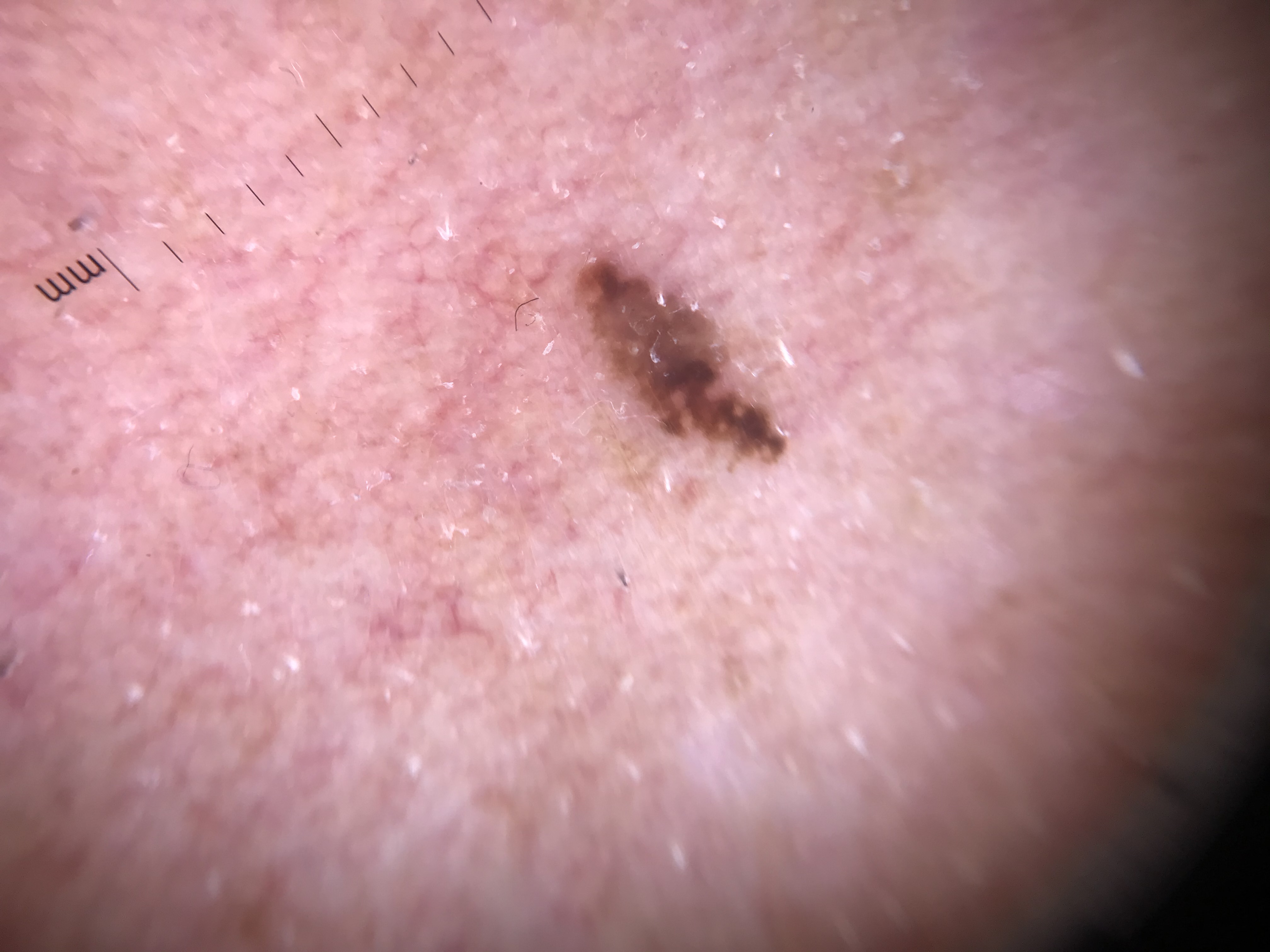  image: dermatoscopy
  diagnosis:
    name: seborrheic keratosis
    code: sk
    malignancy: benign
    super_class: non-melanocytic
    confirmation: expert consensus